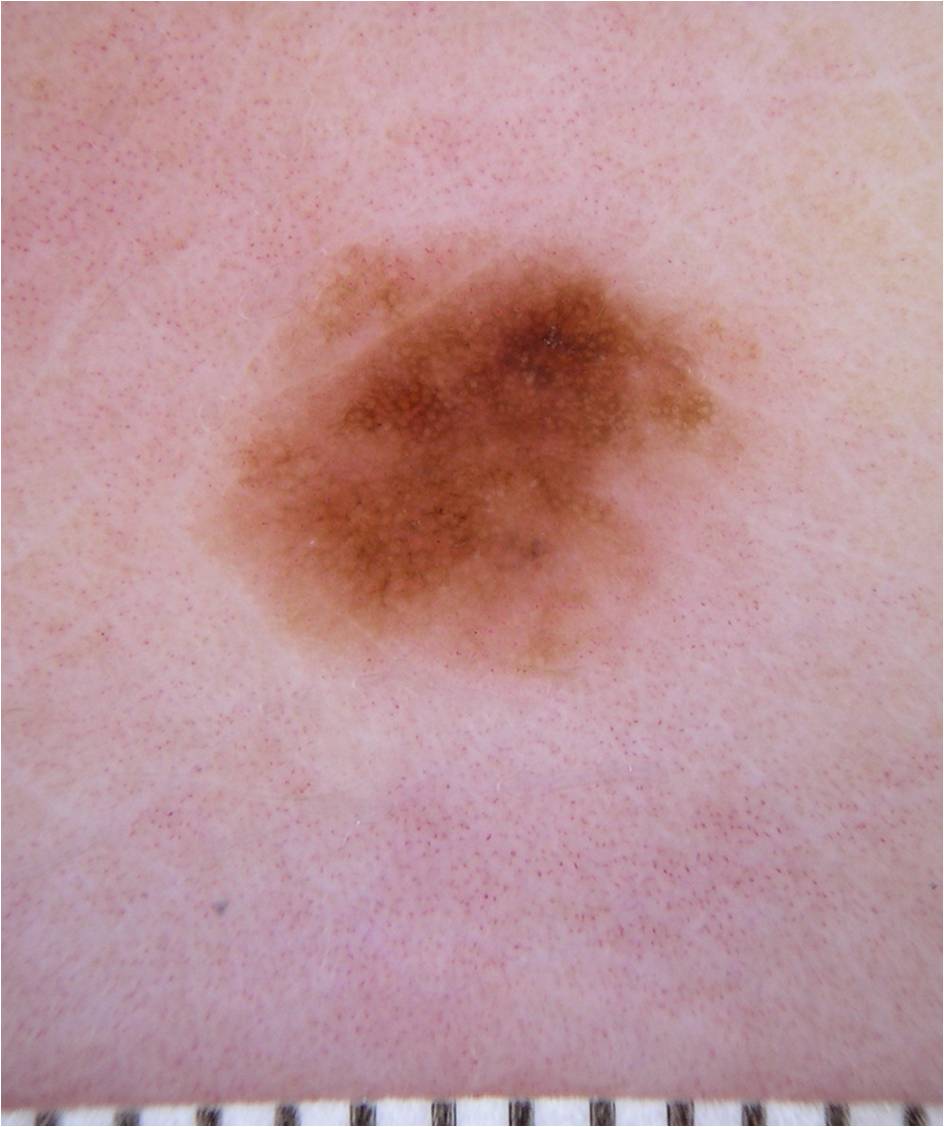modality = dermoscopy
patient = female, aged 38-42
lesion bbox = (205, 233, 757, 677)
extent = moderate
dermoscopic findings = pigment network and milia-like cysts
assessment = a melanoma, a malignancy